A dermoscopy image of a single skin lesion. The patient is a male in their mid- to late 40s.
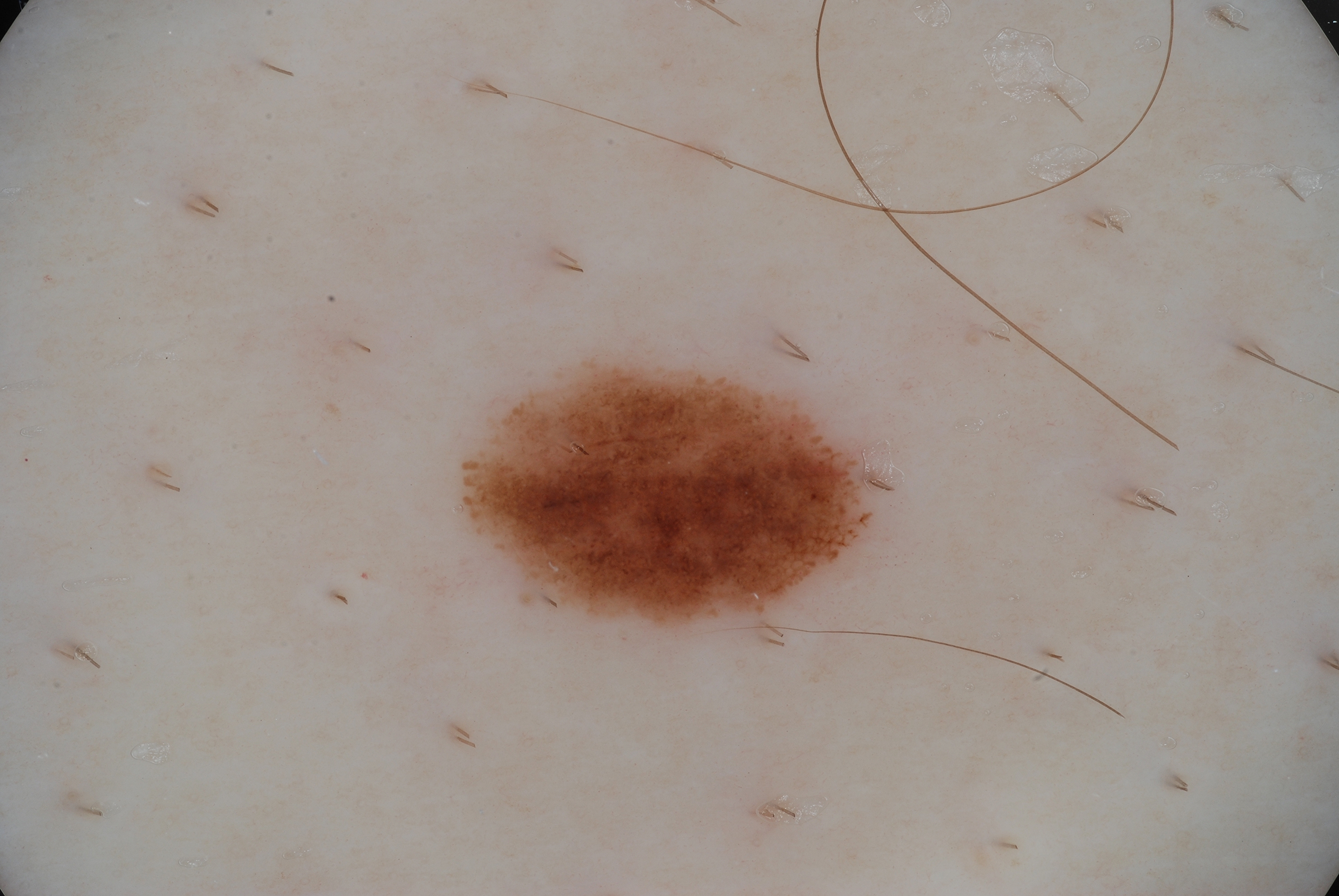Case summary:
- features · pigment network; absent: negative network, streaks, and milia-like cysts
- size · small
- bounding box · x1=471, y1=365, x2=868, y2=630
- assessment · a melanocytic nevus, a benign lesion